An image taken at a distance; the contributor is a male aged 18–29; the leg is involved.
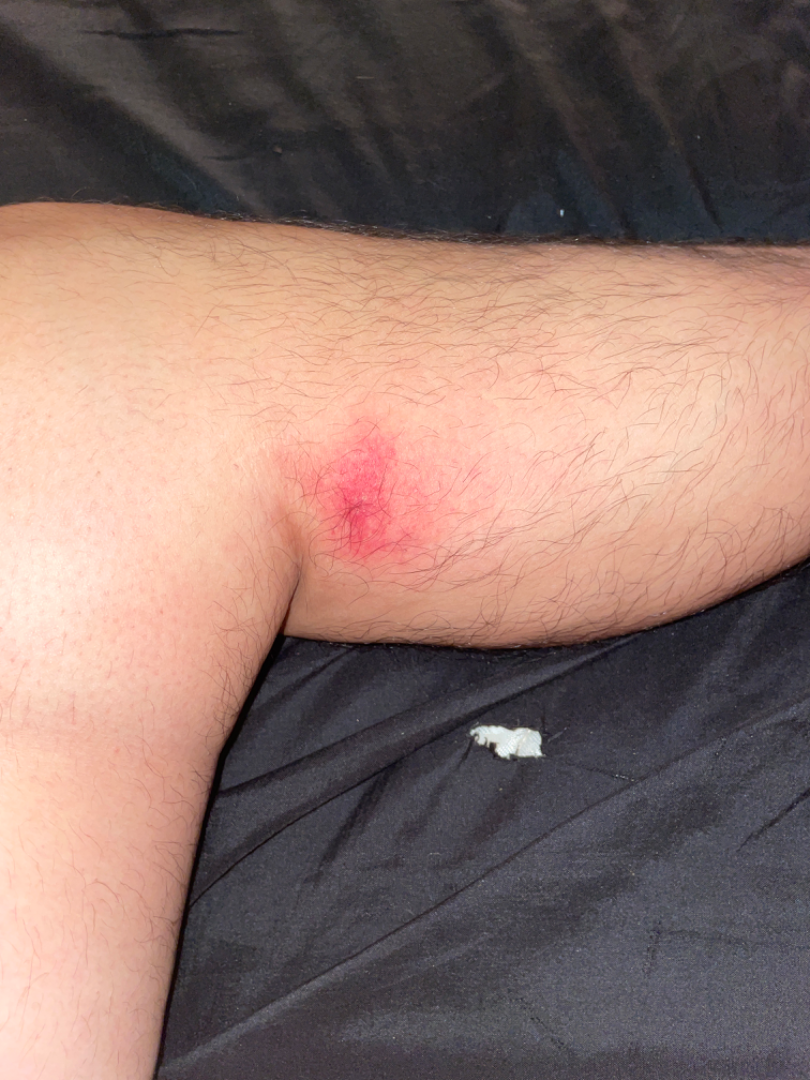On independent review by the dermatologists: most likely Cellulitis; also consider Insect Bite; lower on the differential is Irritant Contact Dermatitis; less likely is Abscess; less probable is Eczema.